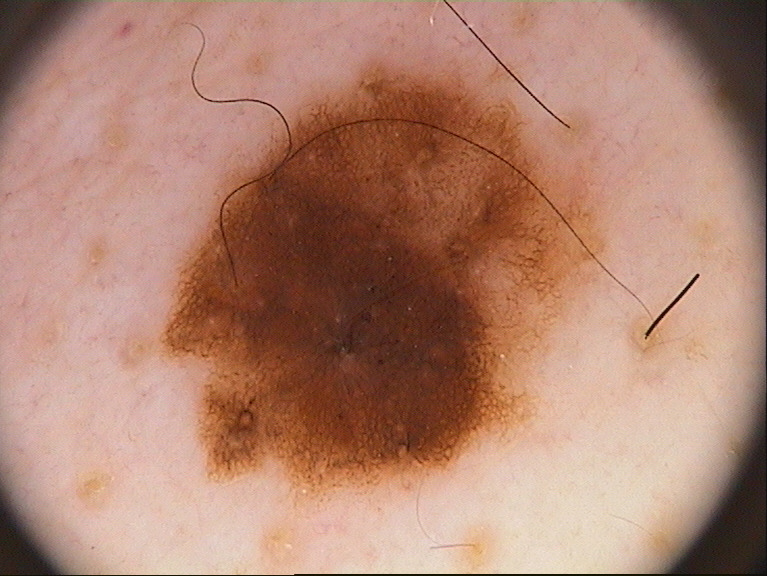| key | value |
|---|---|
| image | dermoscopy of a skin lesion |
| subject | male, aged around 75 |
| size | ~34% of the field |
| bounding box | bbox(159, 53, 621, 514) |
| dermoscopic findings | globules and pigment network; absent: milia-like cysts, streaks, and negative network |
| impression | a melanocytic nevus, a benign skin lesion |